A clinical photograph of a skin lesion; a male patient aged 60 — 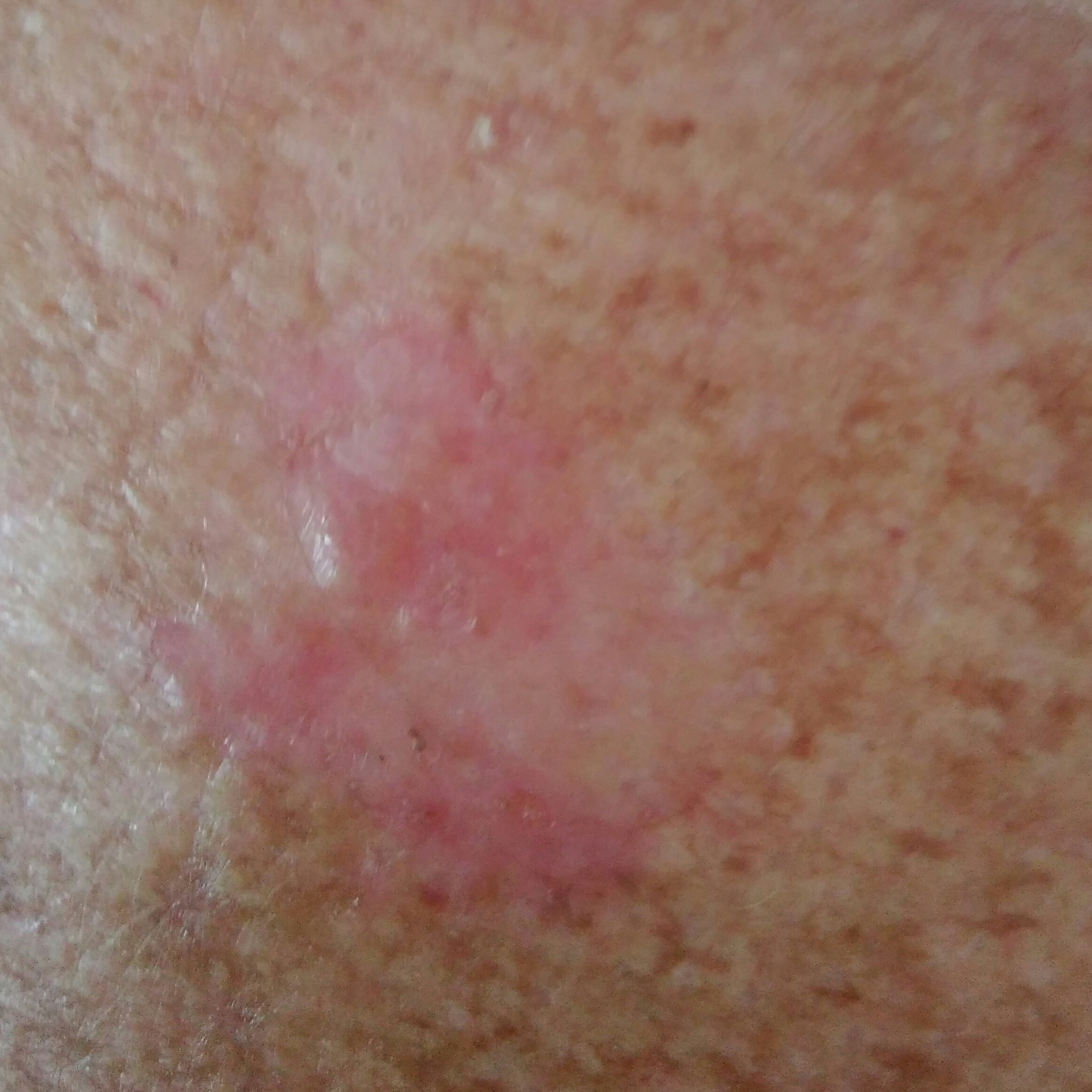Summary: Located on the nose. The lesion is roughly 3 by 3 mm. By the patient's account, the lesion itches. Conclusion: On biopsy, the diagnosis was a malignant lesion — a squamous cell carcinoma.